A dermoscopic view of a skin lesion: 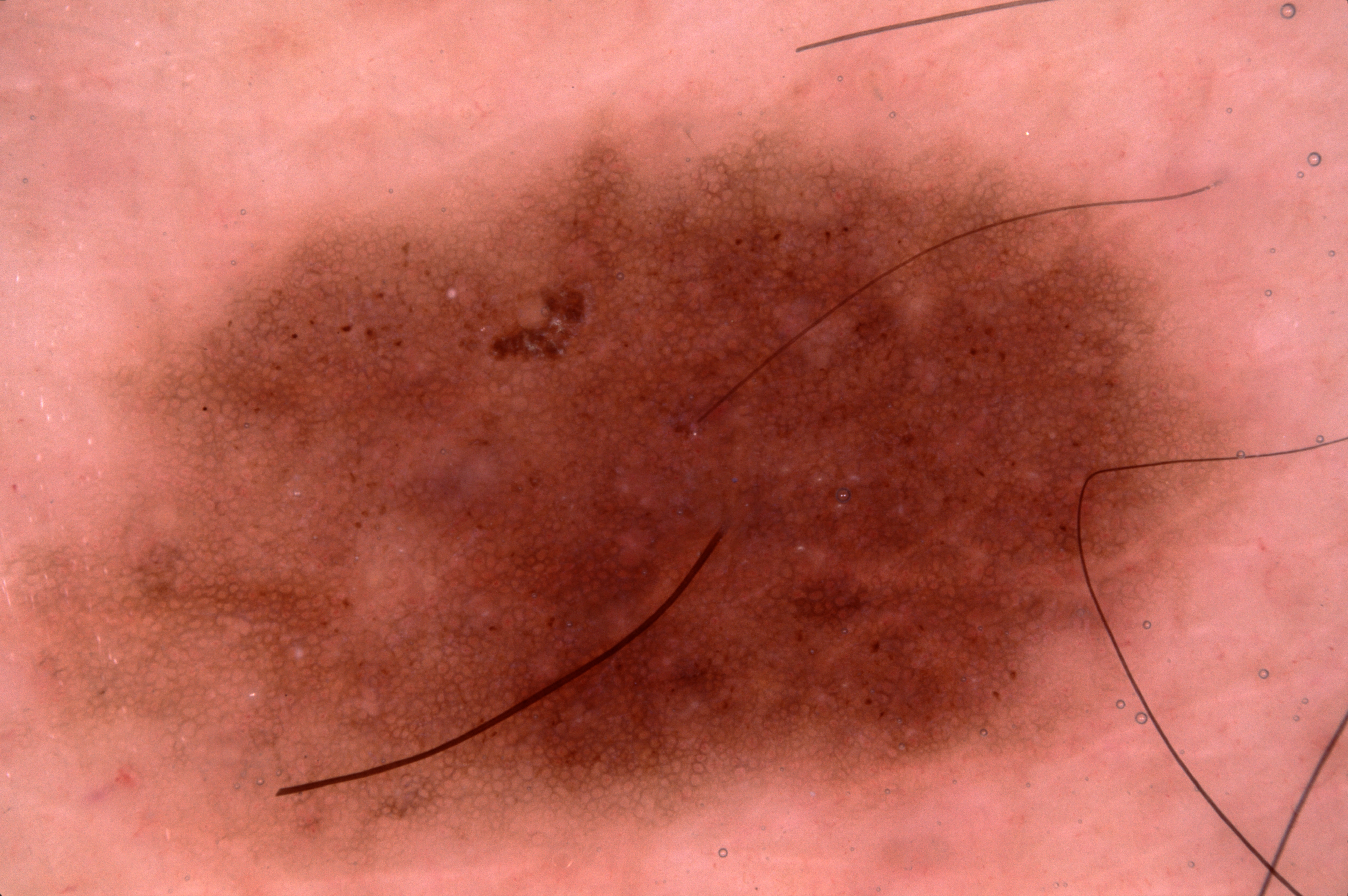The lesion spans left=9, top=95, right=1273, bottom=858. Expert review diagnosed this as a melanocytic nevus, a benign lesion.